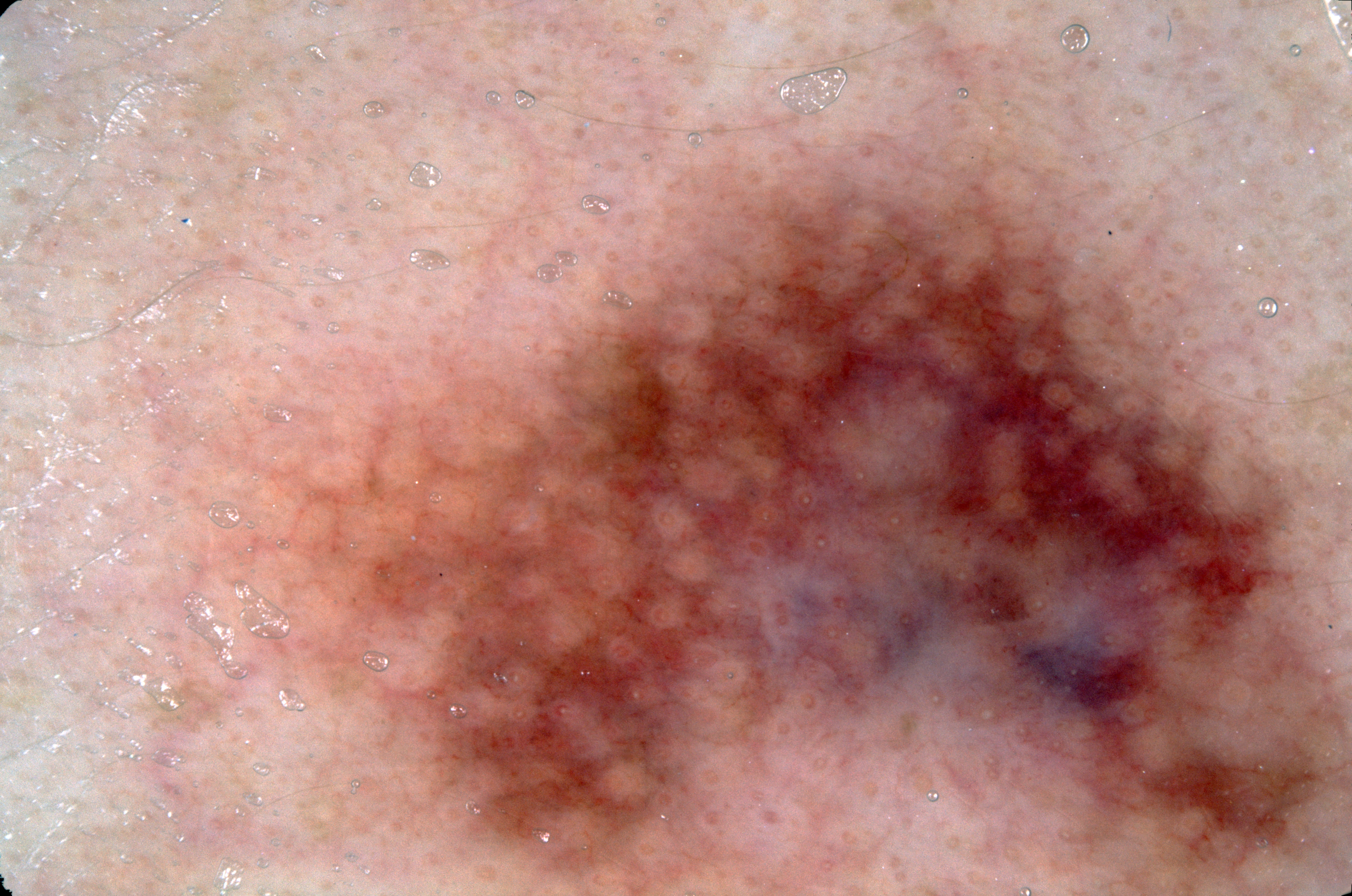Case summary:
A female patient aged 23-27. A dermoscopic close-up of a skin lesion. Dermoscopically, the lesion shows no milia-like cysts, negative network, streaks, or pigment network. In (x1, y1, x2, y2) order, the visible lesion spans box(222, 130, 1343, 893). The lesion takes up about 56% of the image.
Assessment:
Expert review diagnosed this as a melanocytic nevus.